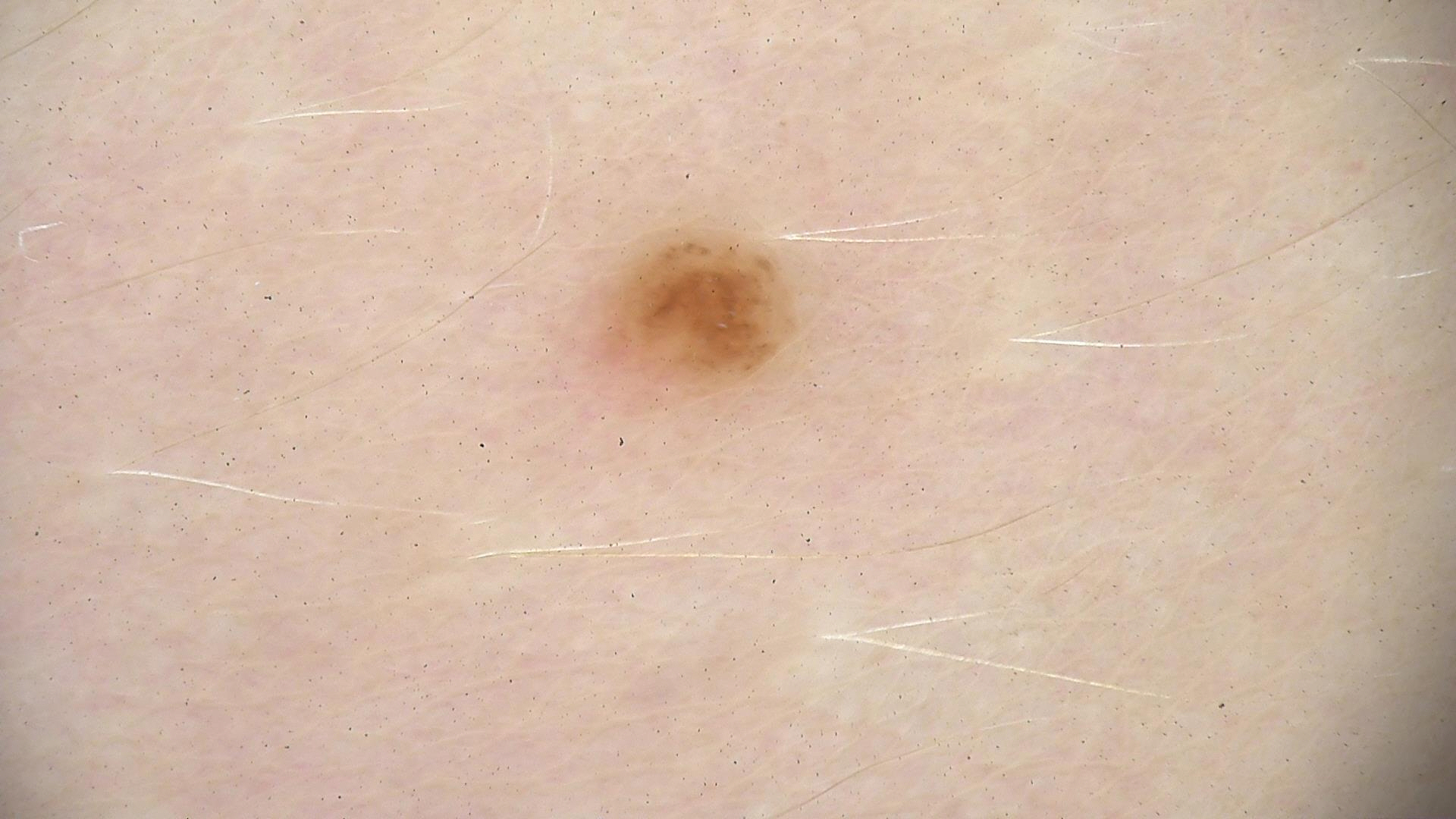image — dermoscopy
label — dysplastic junctional nevus (expert consensus)